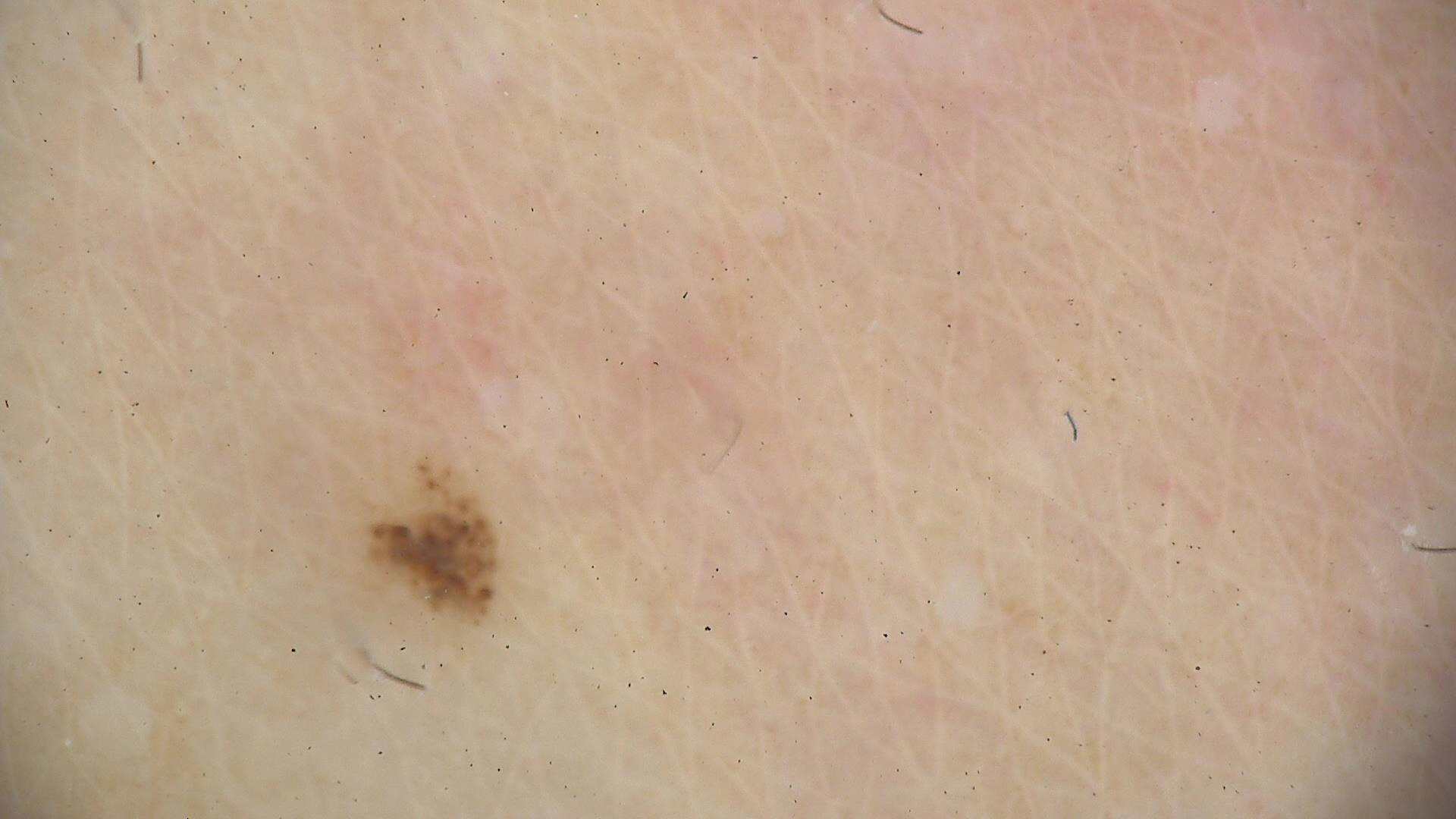The diagnostic label was a dysplastic junctional nevus.